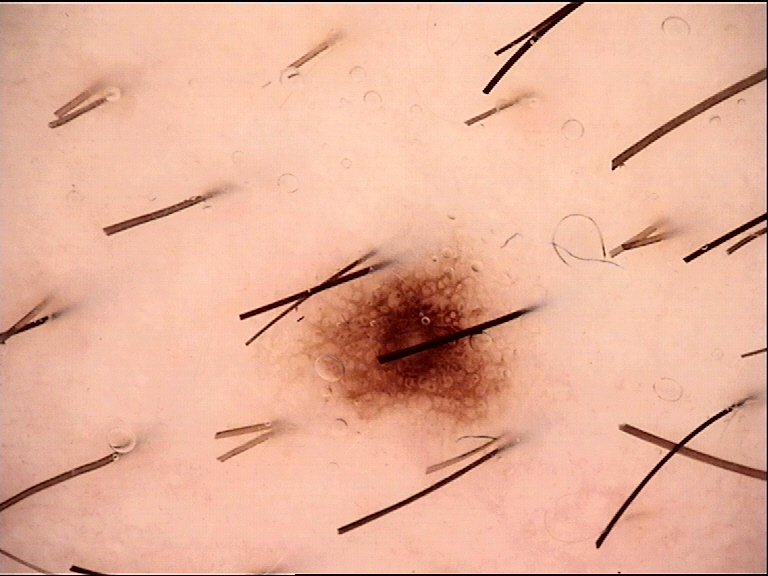A dermoscopic image of a skin lesion. Classified as a dysplastic junctional nevus.